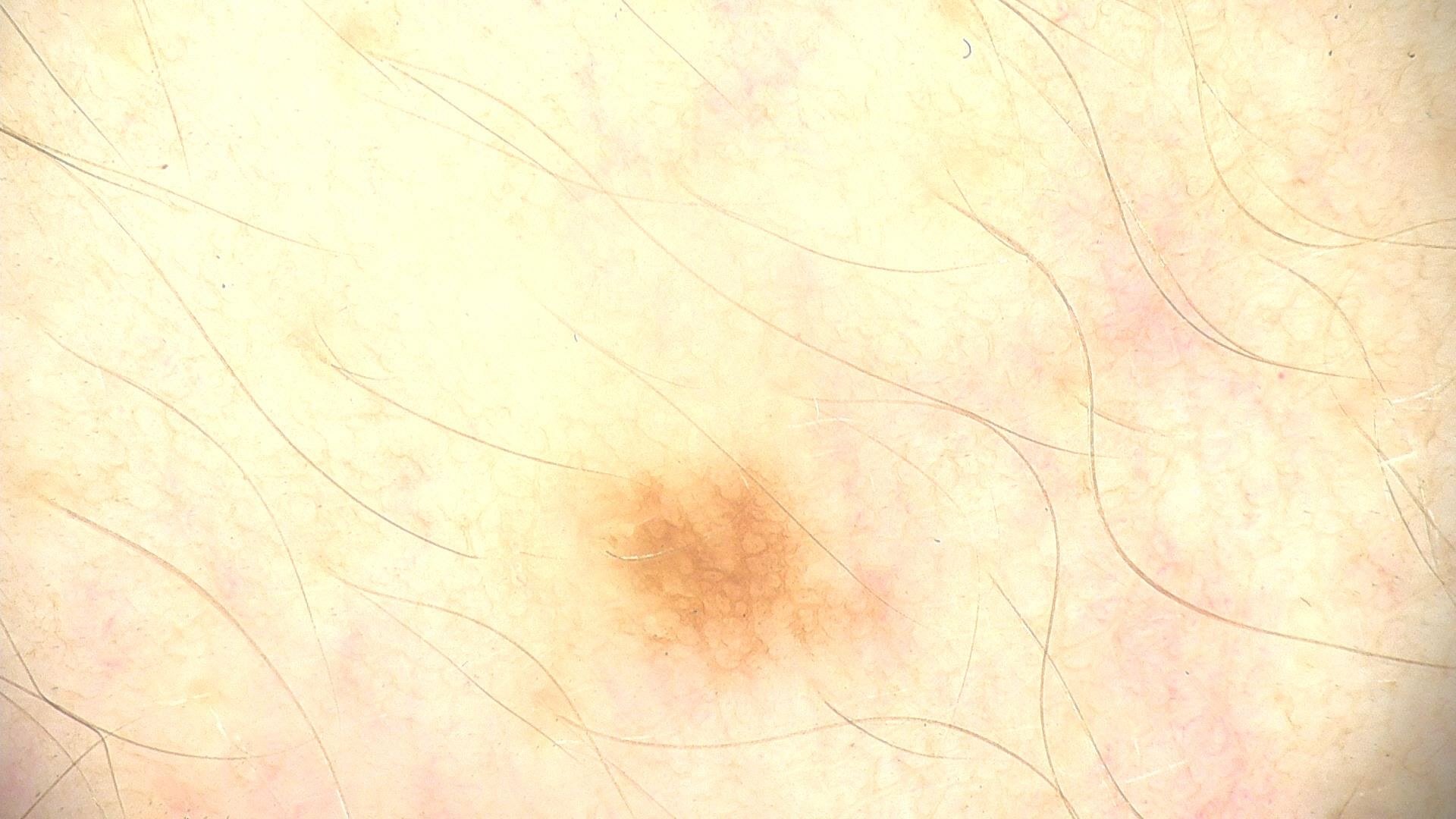diagnostic label: dysplastic junctional nevus (expert consensus).